Close-up view · the patient indicates the lesion is rough or flaky · no constitutional symptoms were reported · the condition has been present for one to four weeks · female contributor, age 18–29 · the lesion involves the leg · the lesion is associated with bothersome appearance · the patient described the issue as a rash: 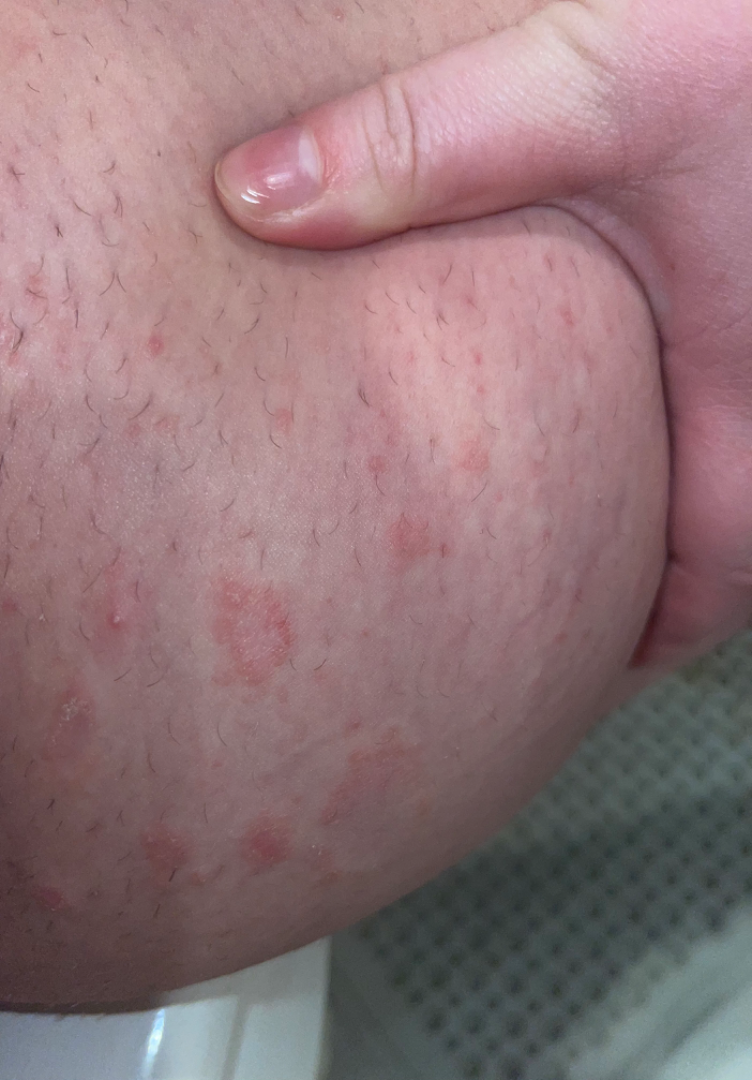assessment: indeterminate from the photograph